Female contributor, age 30–39. An image taken at an angle. The patient described the issue as a rash. FST III. The contributor notes the condition has been present for about one day. The lesion involves the arm and head or neck. Symptoms reported: burning, pain, enlargement and itching. The contributor notes the lesion is raised or bumpy. No relevant systemic symptoms — 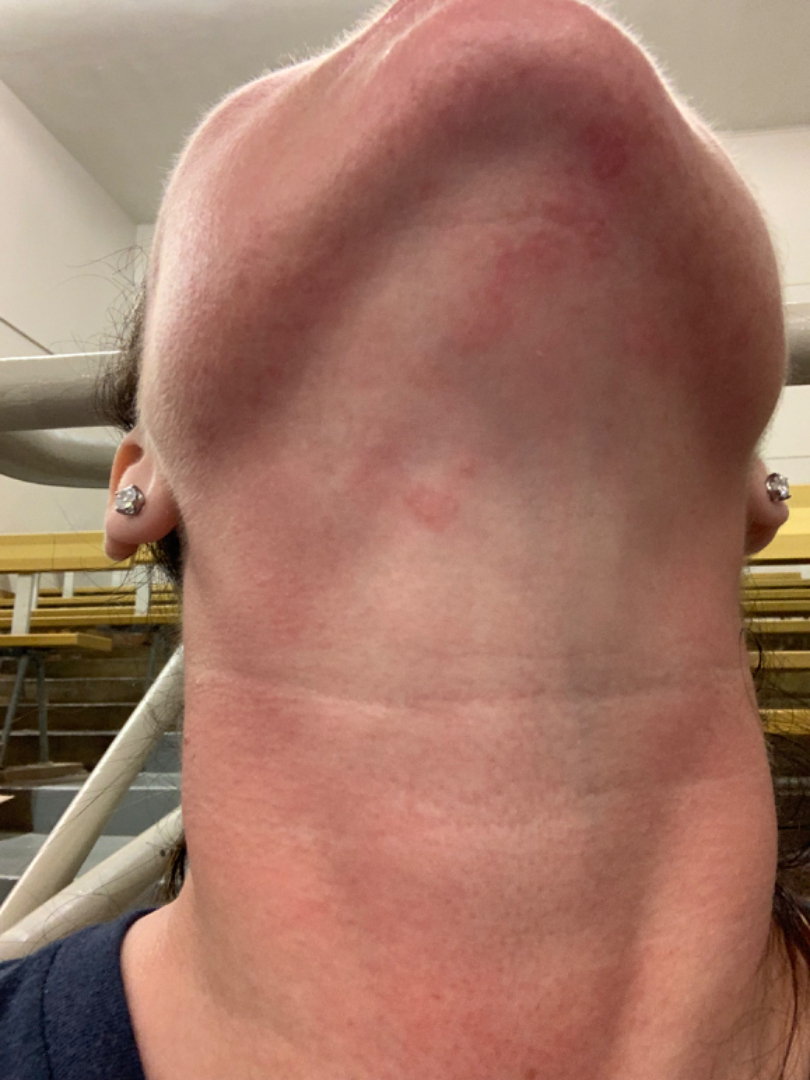Q: What conditions are considered?
A: in keeping with Eczema